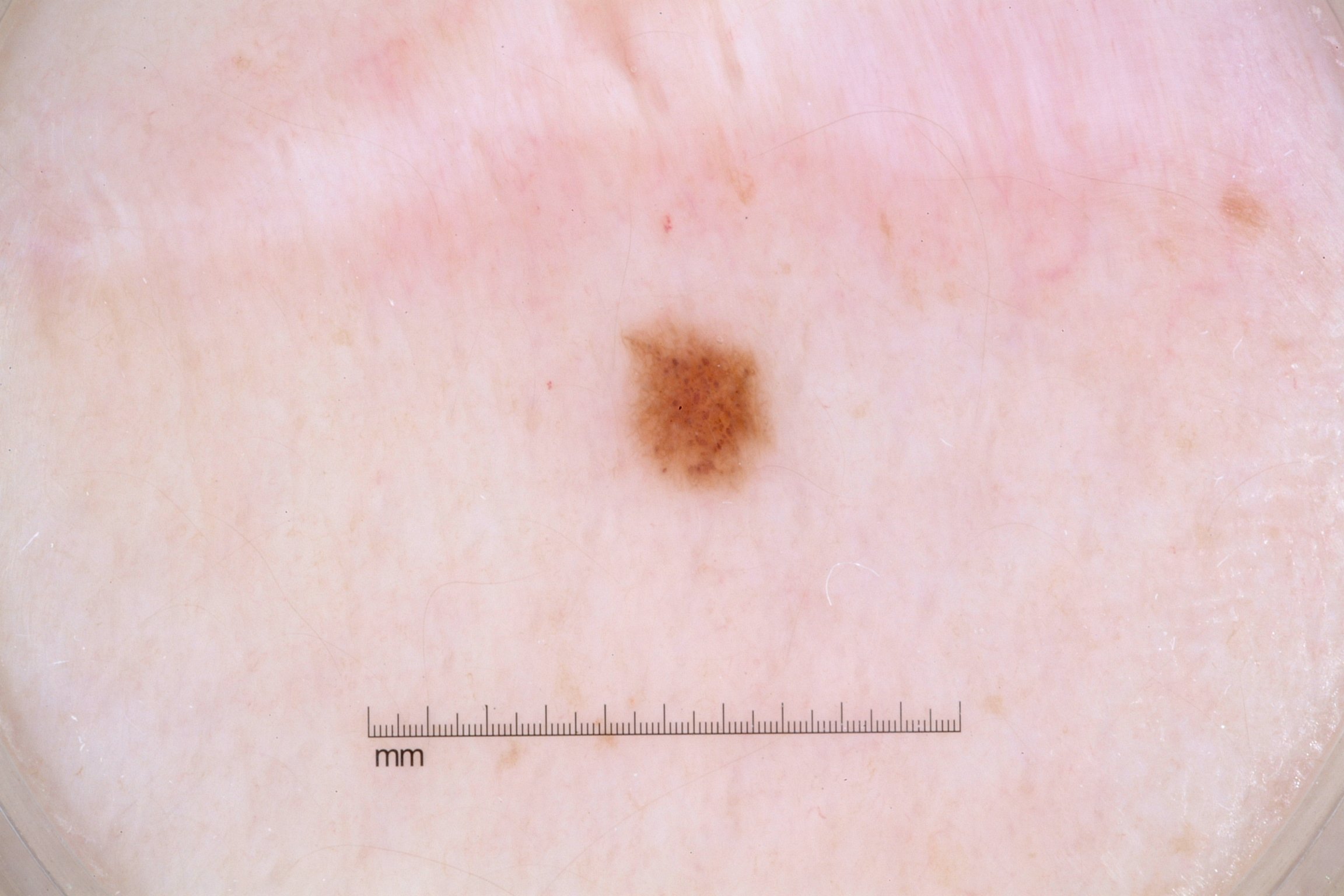A dermatoscopic image of a skin lesion. The subject is a female aged 33 to 37. Dermoscopic review identifies pigment network and milia-like cysts. The lesion's extent is x1=630, y1=322, x2=776, y2=496. The lesion covers approximately 2% of the dermoscopic field. Expert review diagnosed this as a melanocytic nevus, a benign skin lesion.